A skin lesion imaged with a dermatoscope — 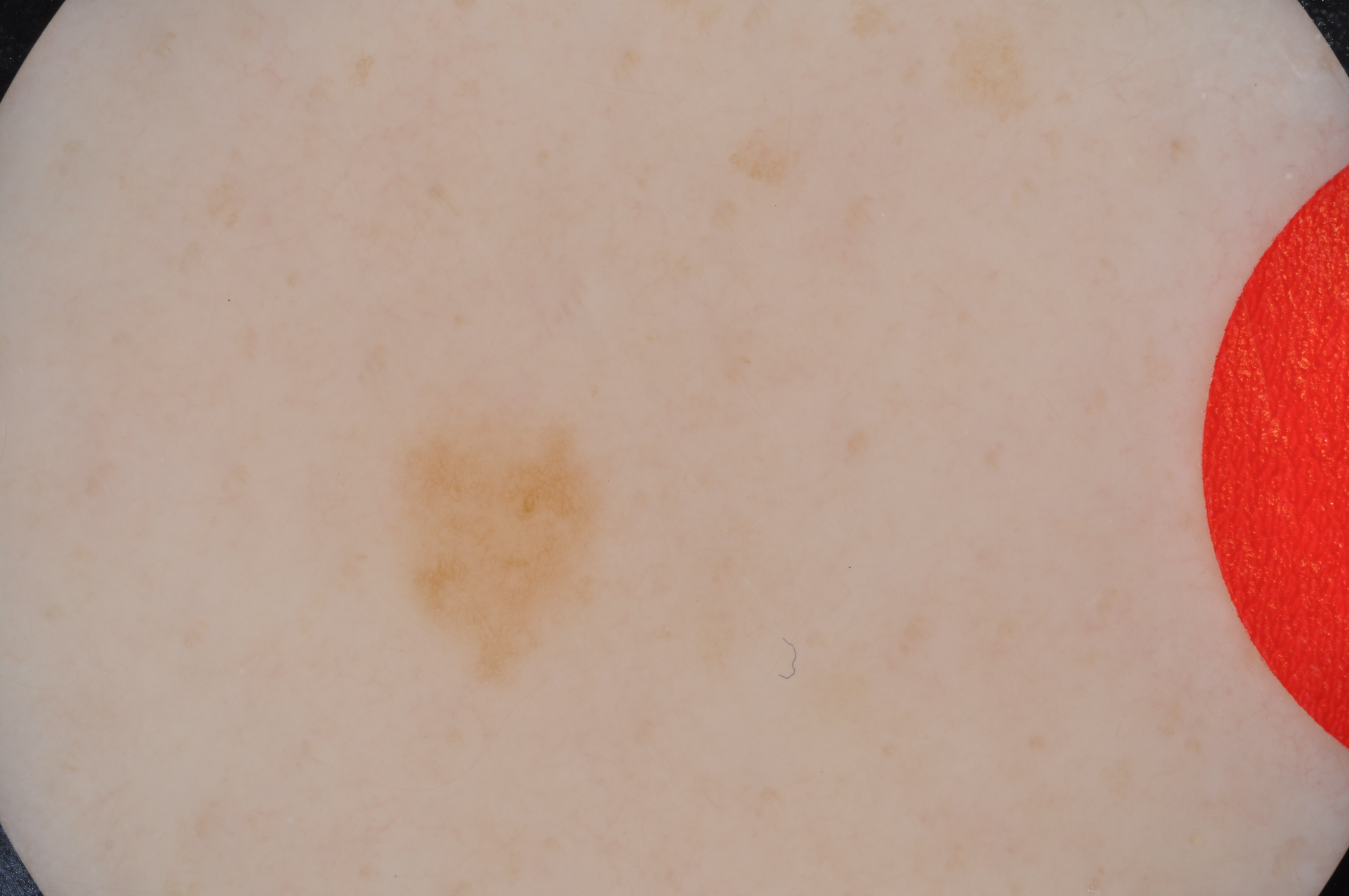Dermoscopic assessment notes no streaks or globules. The visible lesion spans 373/389/629/699. The lesion takes up about 5% of the image. The lesion was assessed as a benign skin lesion.